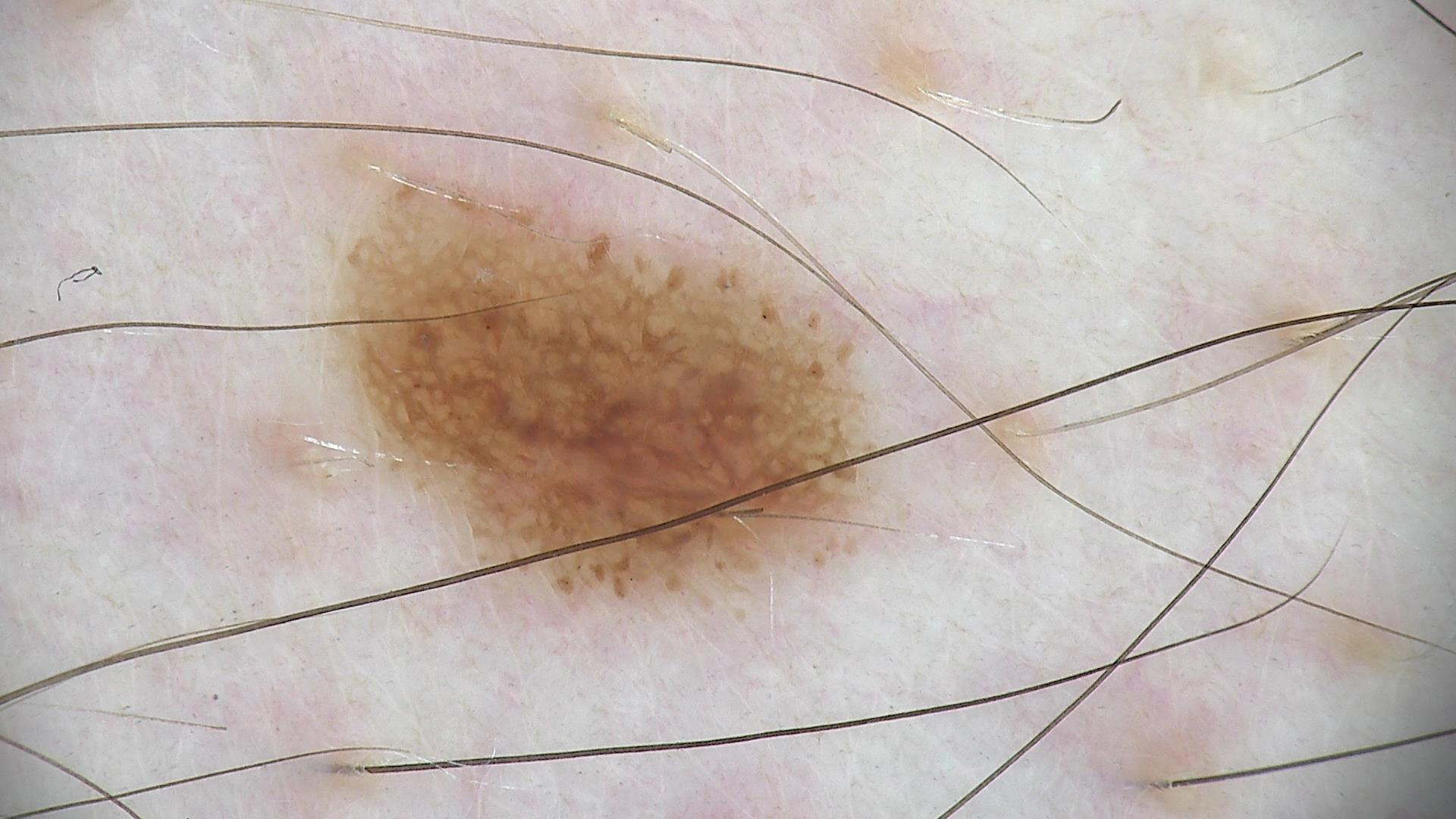Case:
– modality — dermoscopy
– label — dysplastic junctional nevus (expert consensus)